The patient is a male about 60 years old; a dermoscopy image of a single skin lesion:
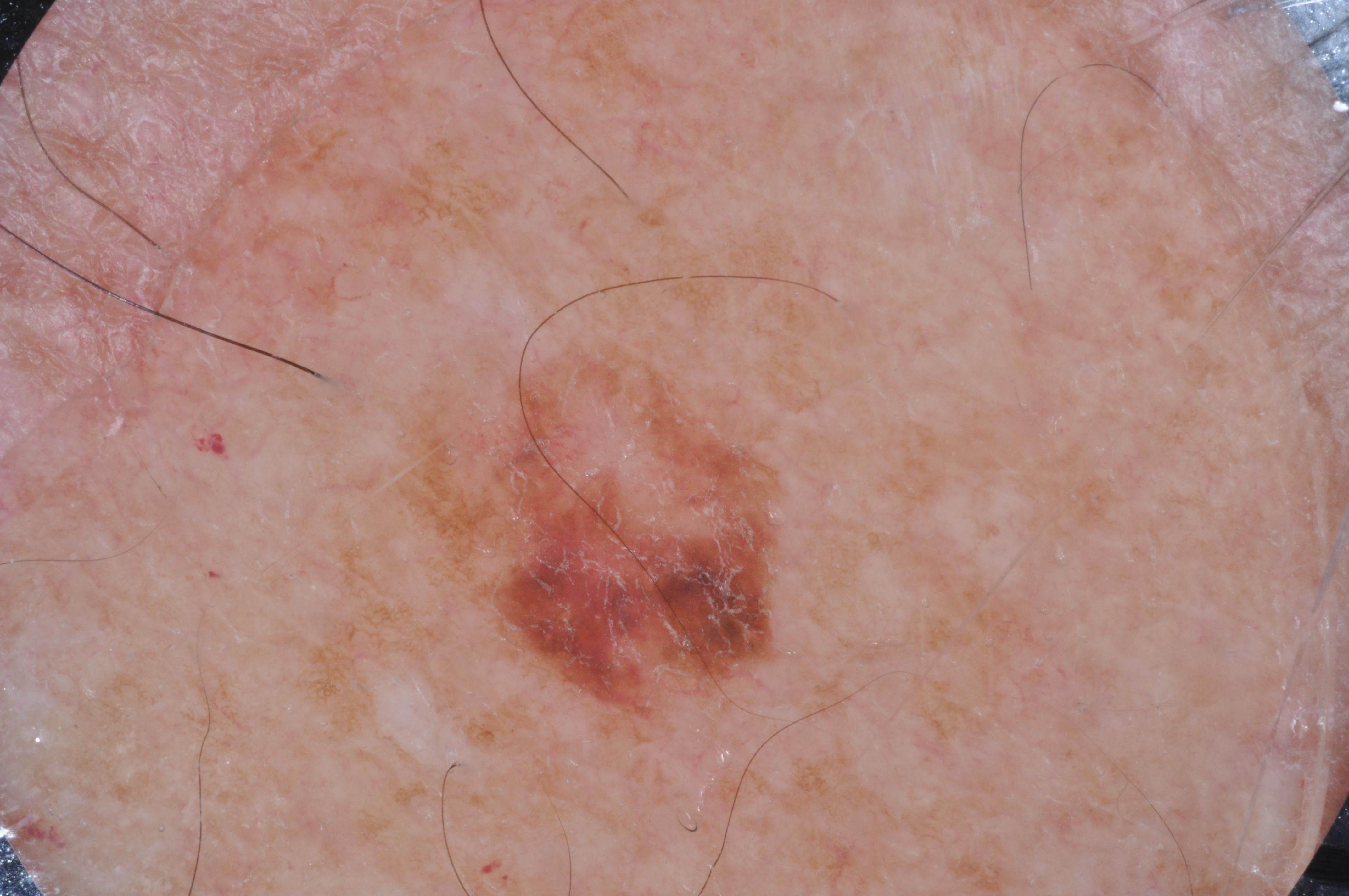Case summary: The lesion takes up about 10% of the image. The lesion spans x1=397, y1=323, x2=796, y2=742. The dermoscopic pattern shows pigment network. Conclusion: Histopathologically confirmed as a melanoma.